A skin lesion imaged with a dermatoscope: 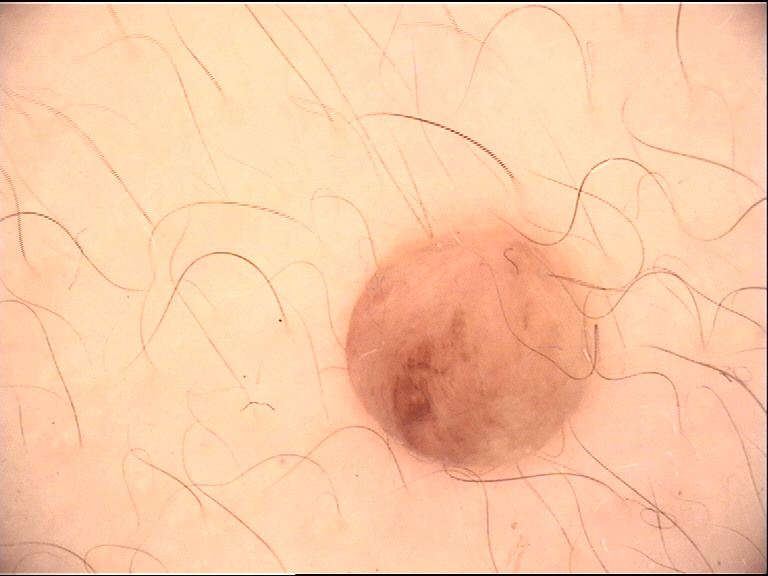label = dermal nevus (expert consensus).